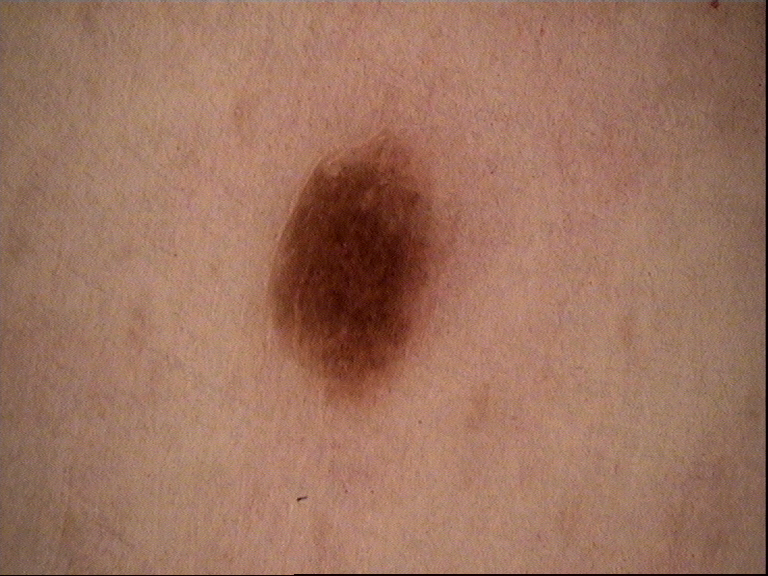diagnostic label=junctional nevus (expert consensus).